Symptoms reported: itching. The patient reports the condition has been present for less than one week. Close-up view. The lesion is described as raised or bumpy. The contributor is a male aged 30–39.
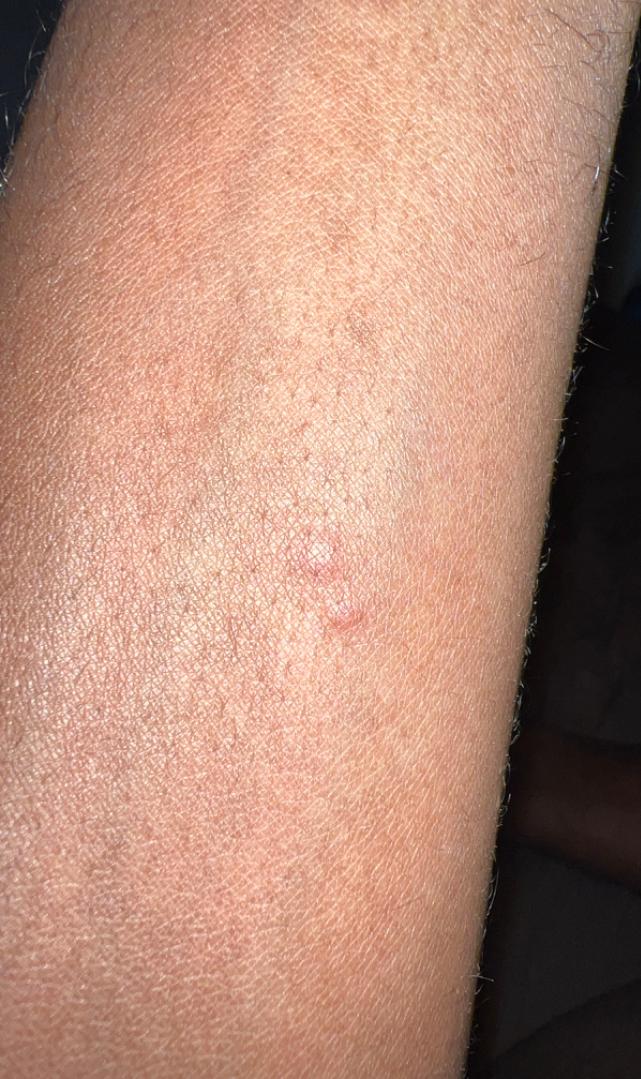differential diagnosis = favoring Insect Bite; possibly Allergic Contact Dermatitis.